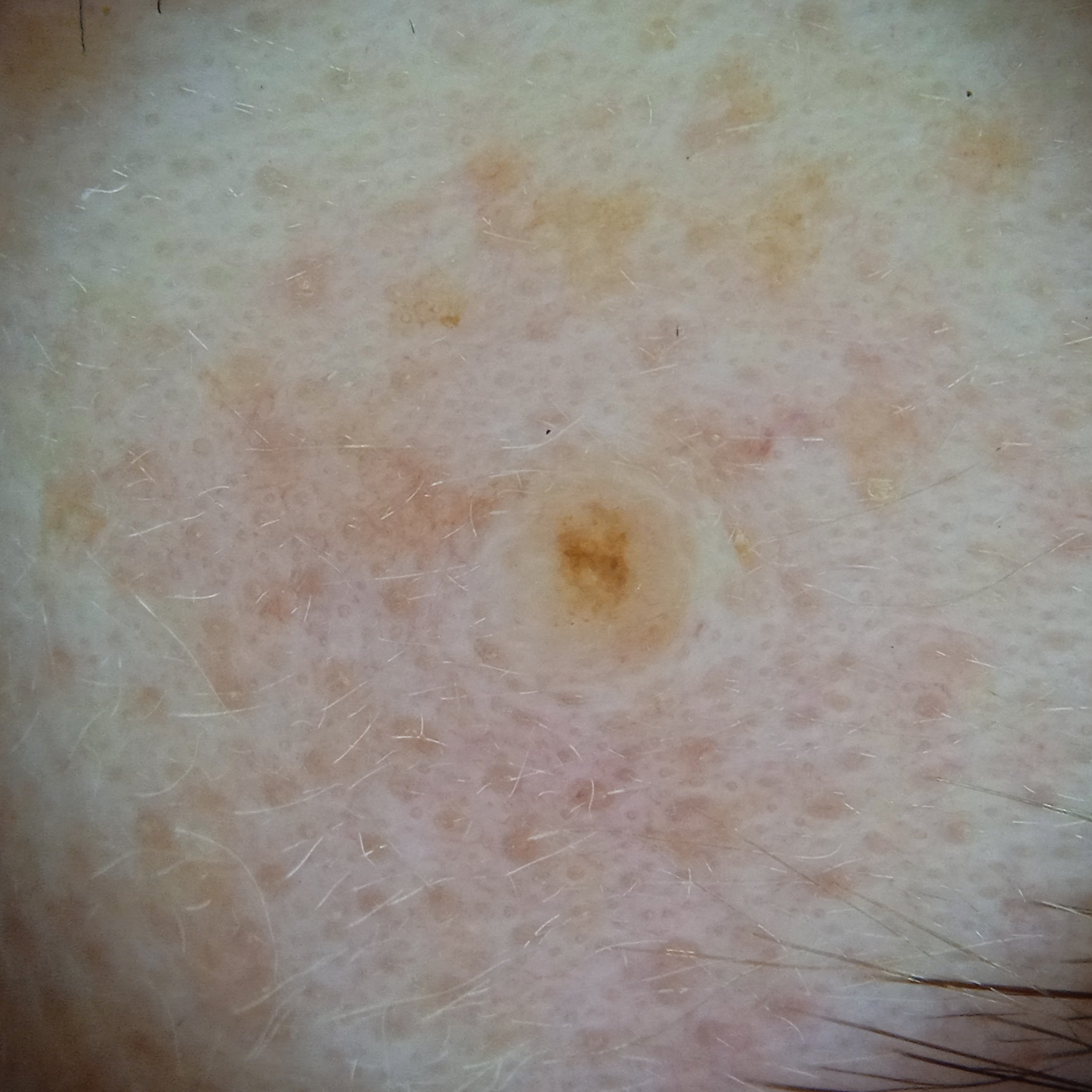The lesion was assessed as a melanocytic nevus.